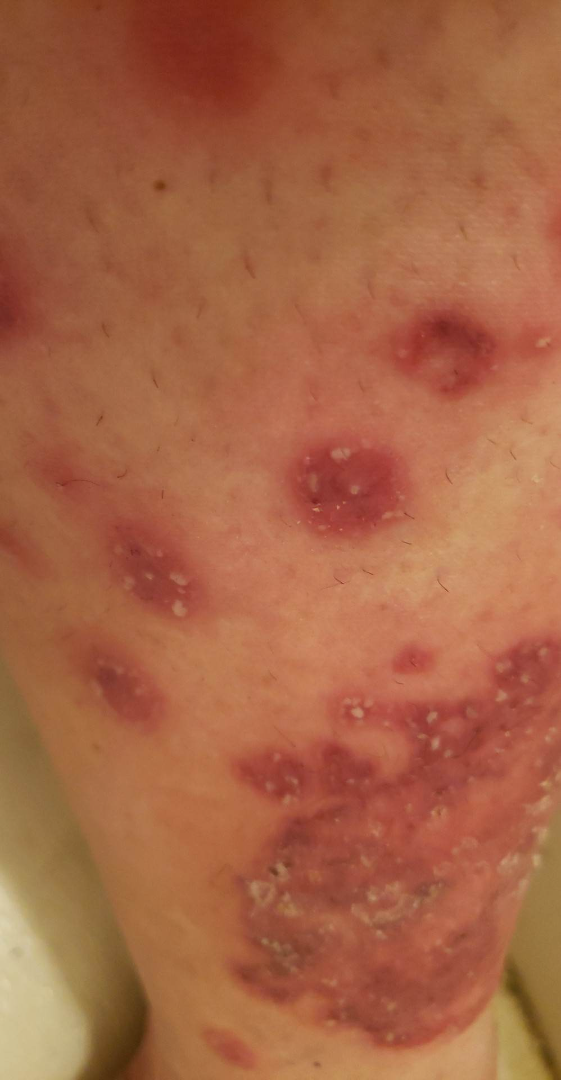Q: Anatomic location?
A: leg
Q: Who is the patient?
A: female, age 40–49
Q: What is the framing?
A: at an angle
Q: What is the differential diagnosis?
A: three dermatologists each reviewed the case: Psoriasis, Deep fungal infection and Eczema were each considered, in no particular order